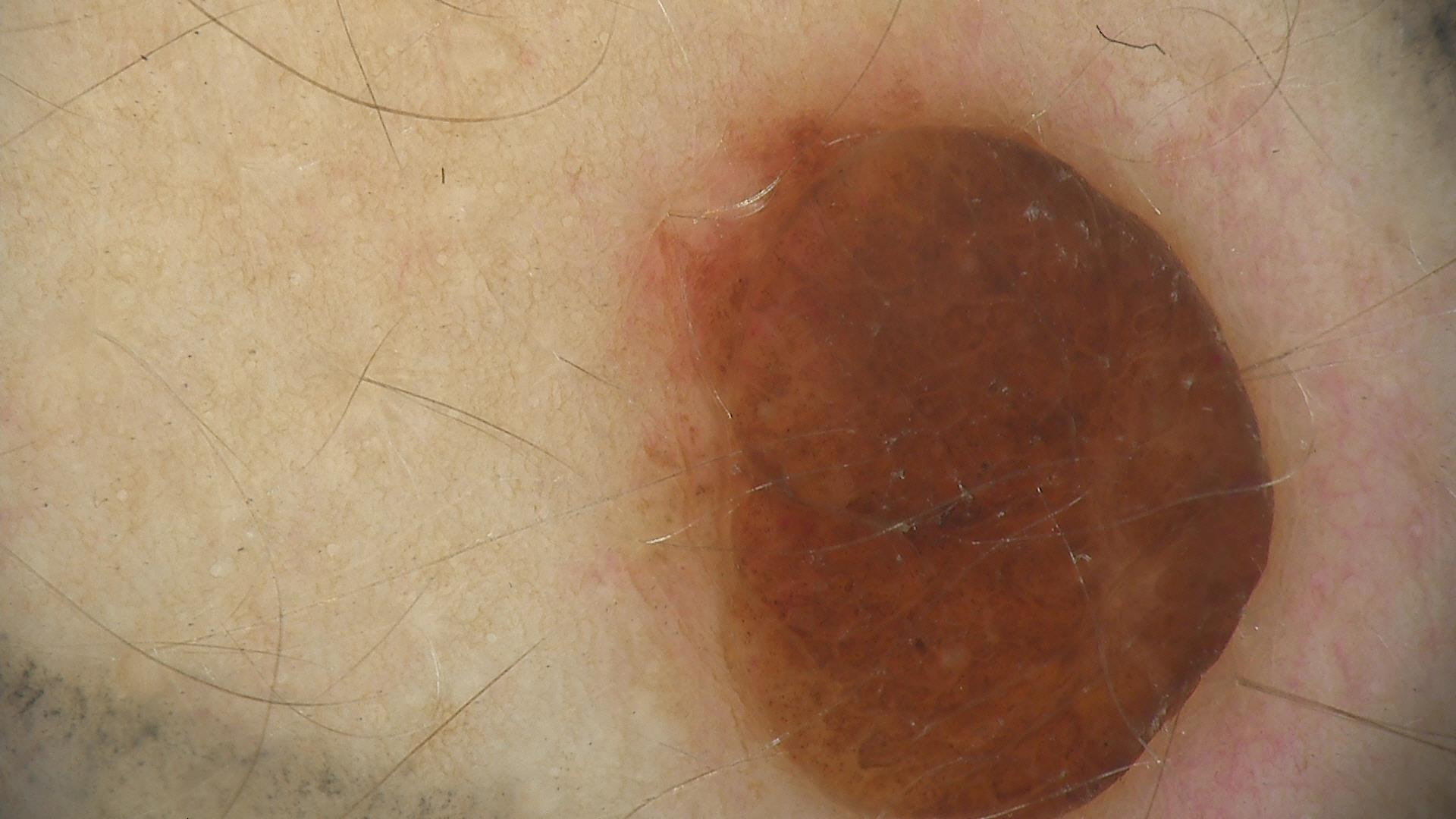{"diagnosis": {"name": "dermal nevus", "code": "db", "malignancy": "benign", "super_class": "melanocytic", "confirmation": "expert consensus"}}